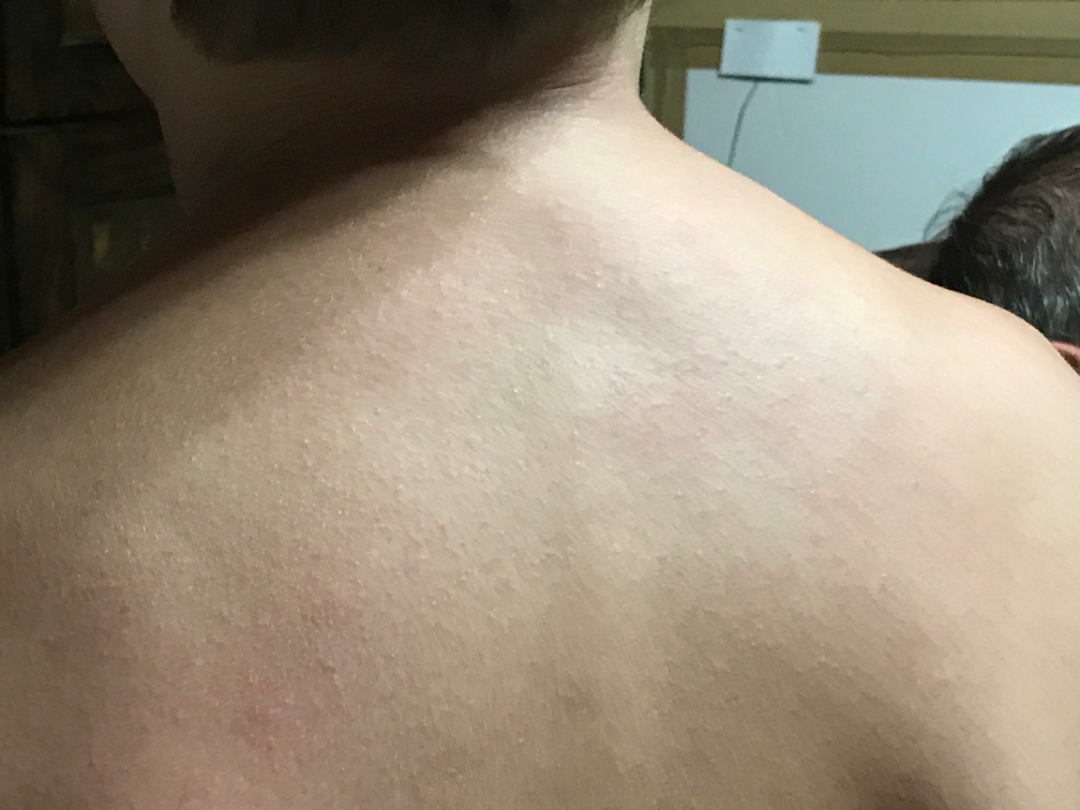Background: Located on the arm and head or neck. The patient considered this a rash. The lesion is associated with bothersome appearance. Present for about one day. This is a close-up image. Fitzpatrick IV; lay graders estimated 3 on the MST. Findings: The differential is split between Miliaria and Folliculitis.